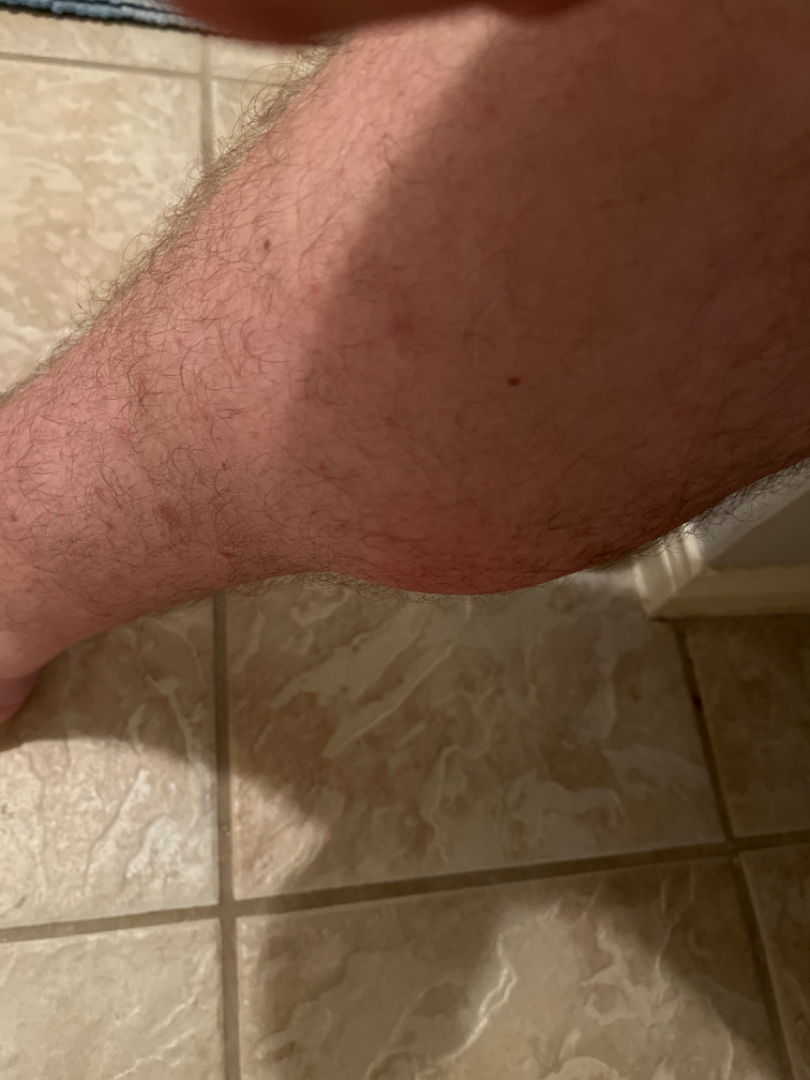Review: No differential diagnosis could be assigned on photographic review.